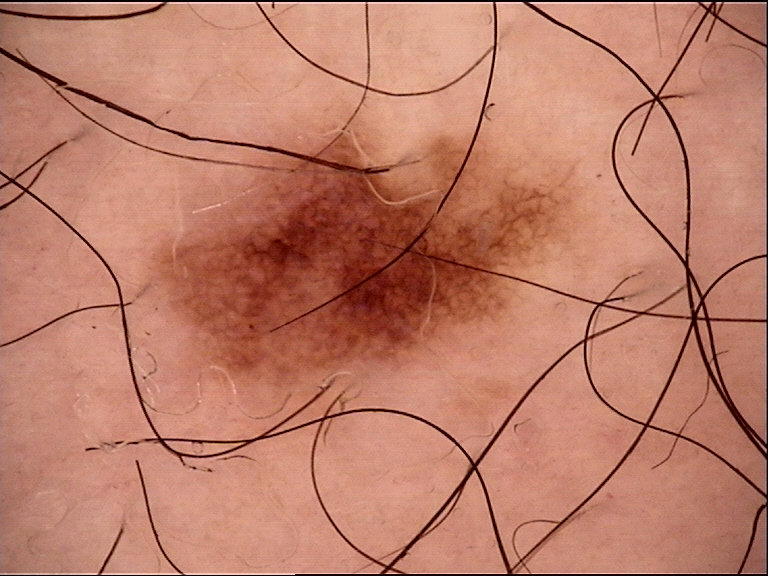Summary:
A dermoscopic image of a skin lesion.
Impression:
Consistent with a dysplastic junctional nevus.